Dermoscopy of a skin lesion.
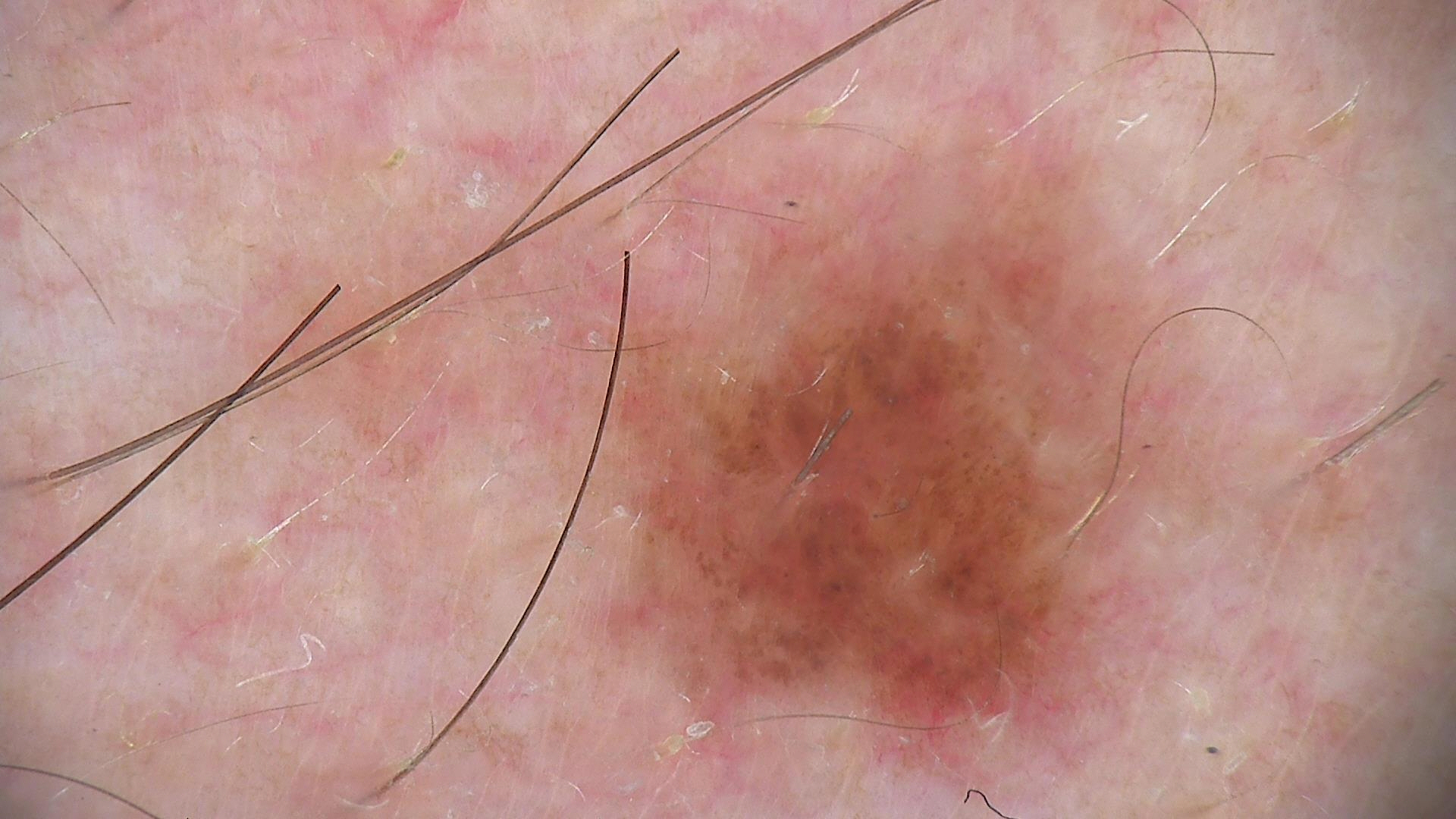diagnostic label: dysplastic junctional nevus (expert consensus).